The patient was assessed as FST II. A dermoscopic close-up of a skin lesion.
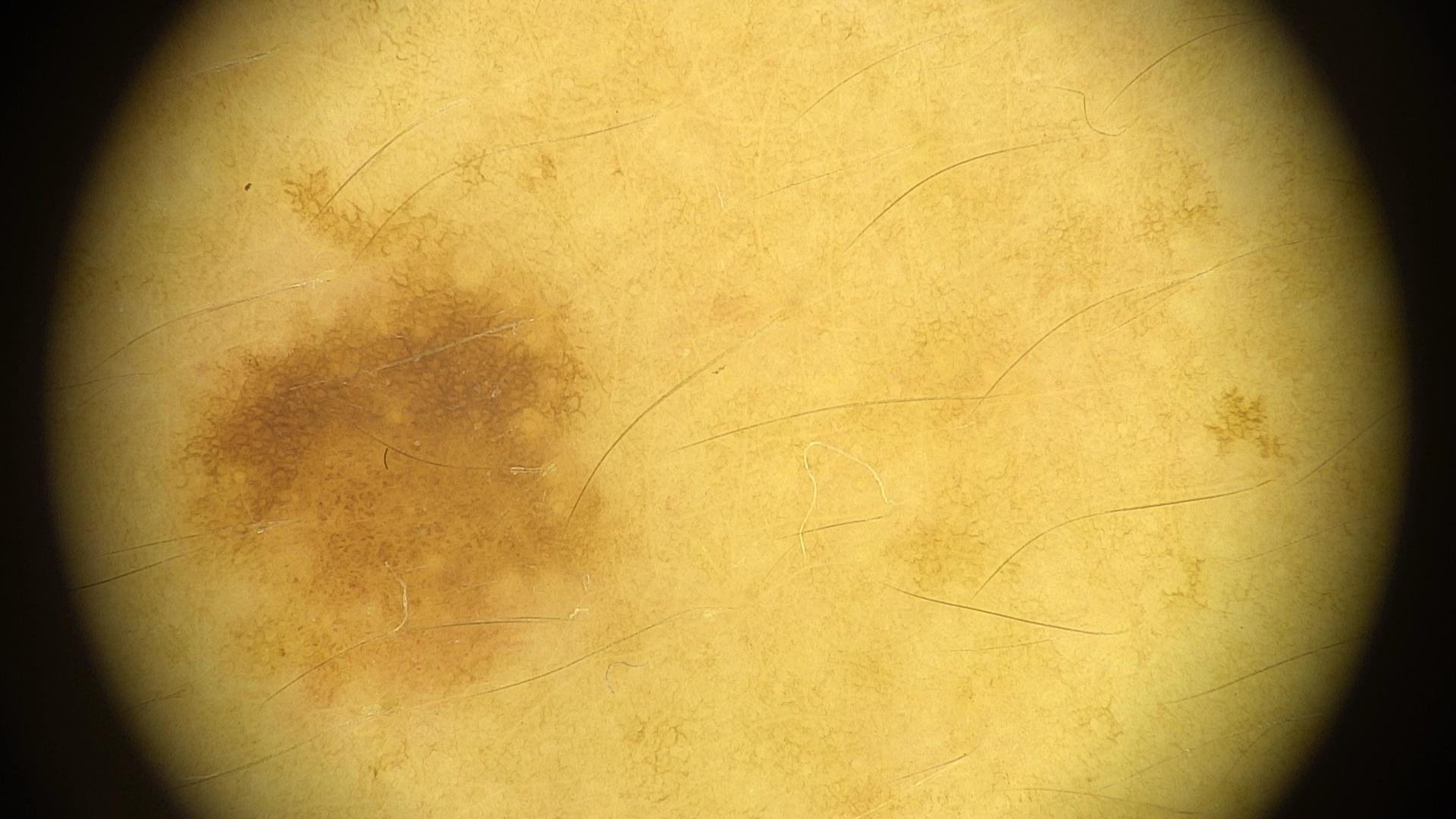Findings: The lesion was found on the trunk (the posterior trunk). Assessment: The diagnostic impression was a melanocytic lesion — a nevus.